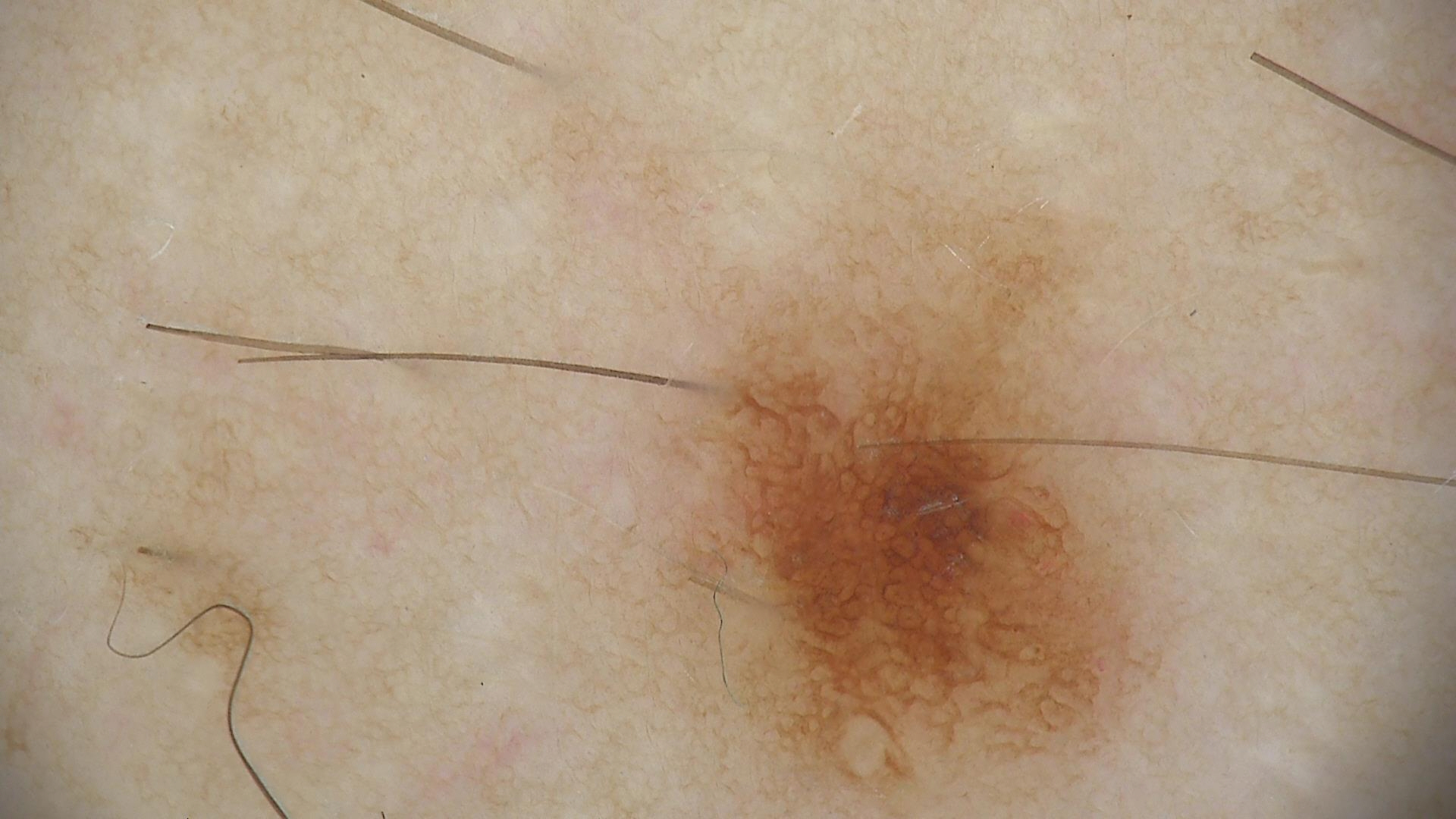assessment: dysplastic junctional nevus (expert consensus).